Dermoscopy of a skin lesion. The patient is a female aged approximately 55:
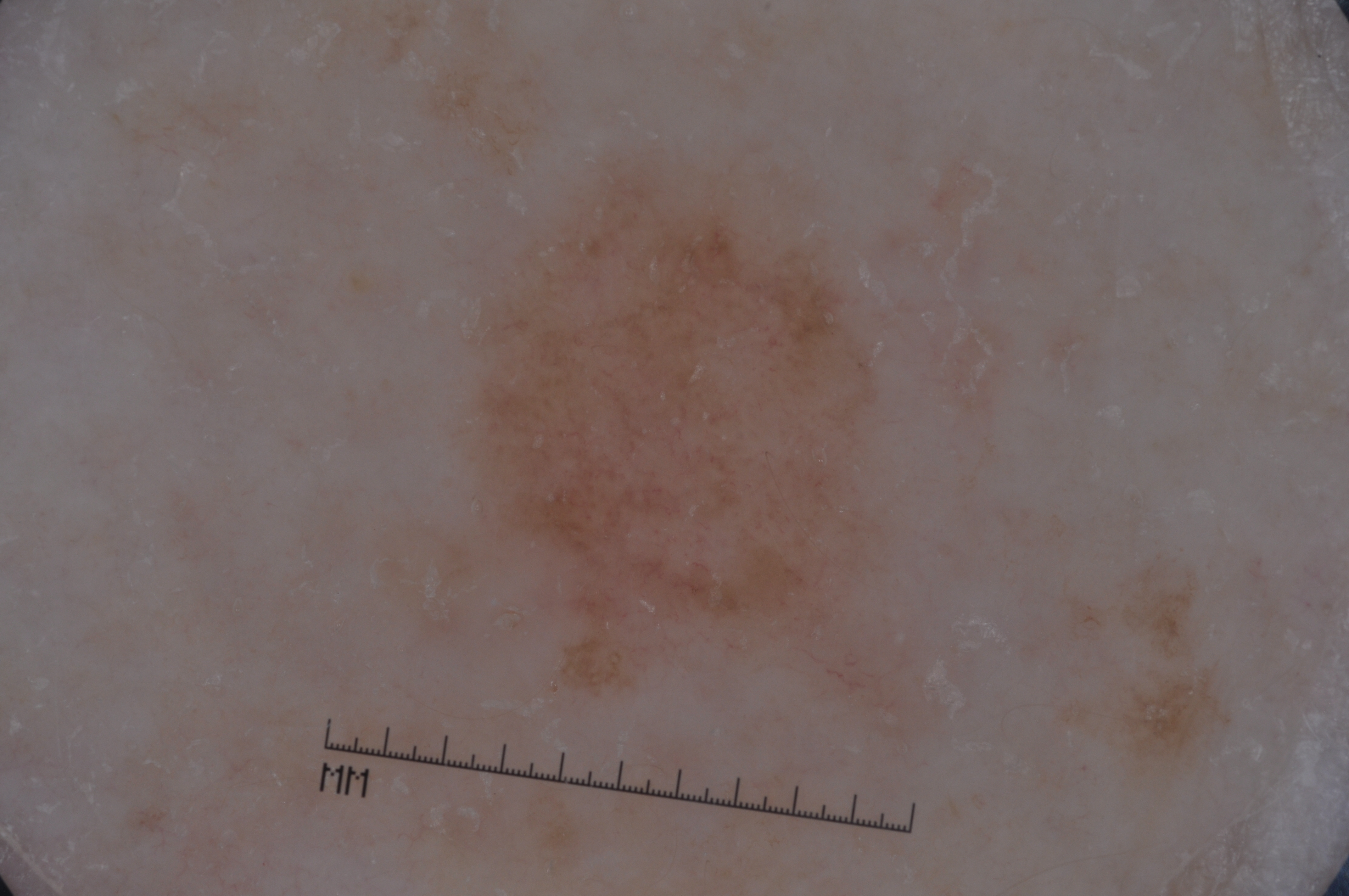* bounding box — x1=459 y1=152 x2=900 y2=697
* dermoscopic features assessed but absent — negative network, pigment network, streaks, and milia-like cysts
* diagnostic label — a melanoma, a skin cancer